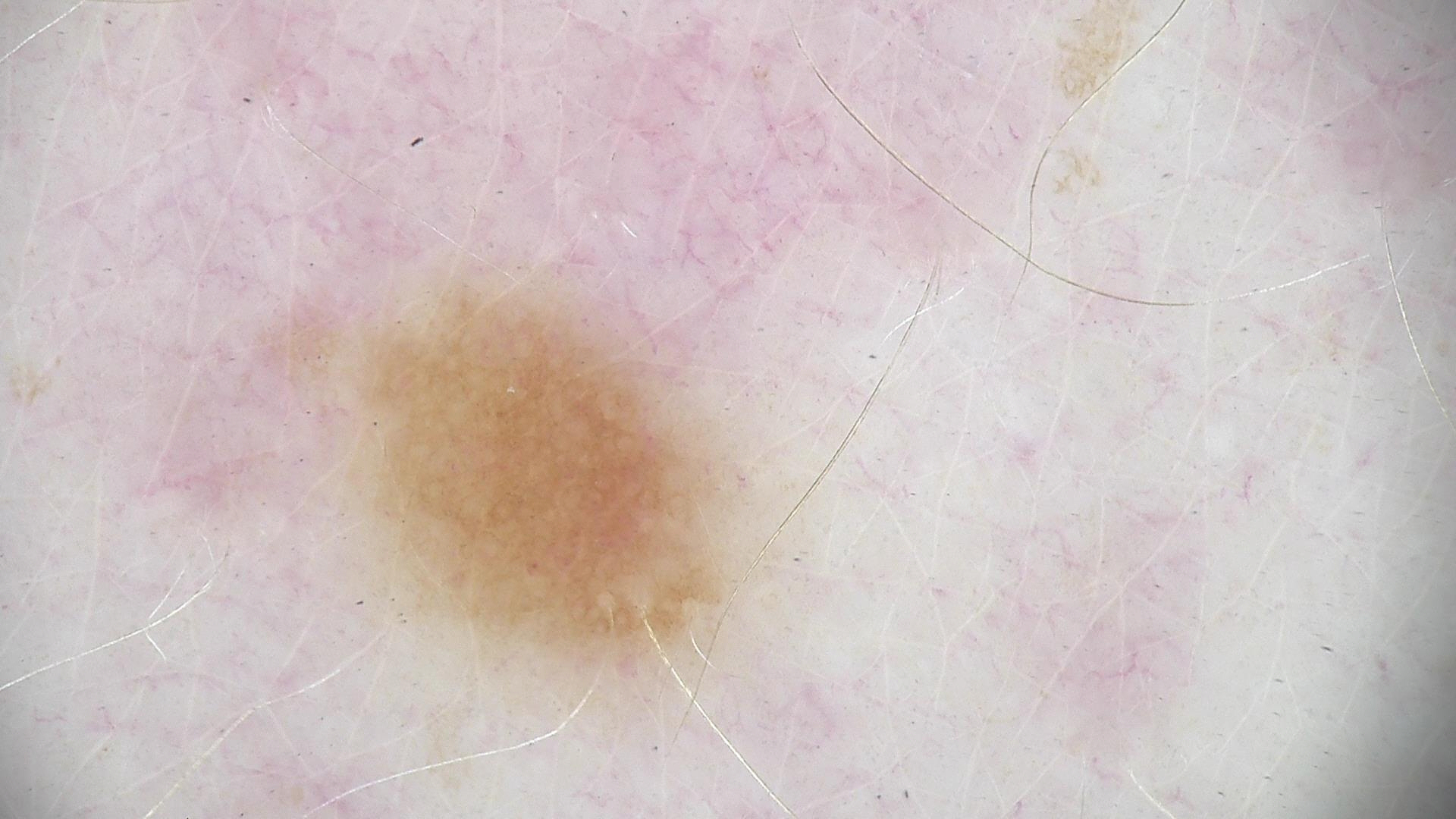modality = dermatoscopy
diagnosis = dysplastic junctional nevus (expert consensus)